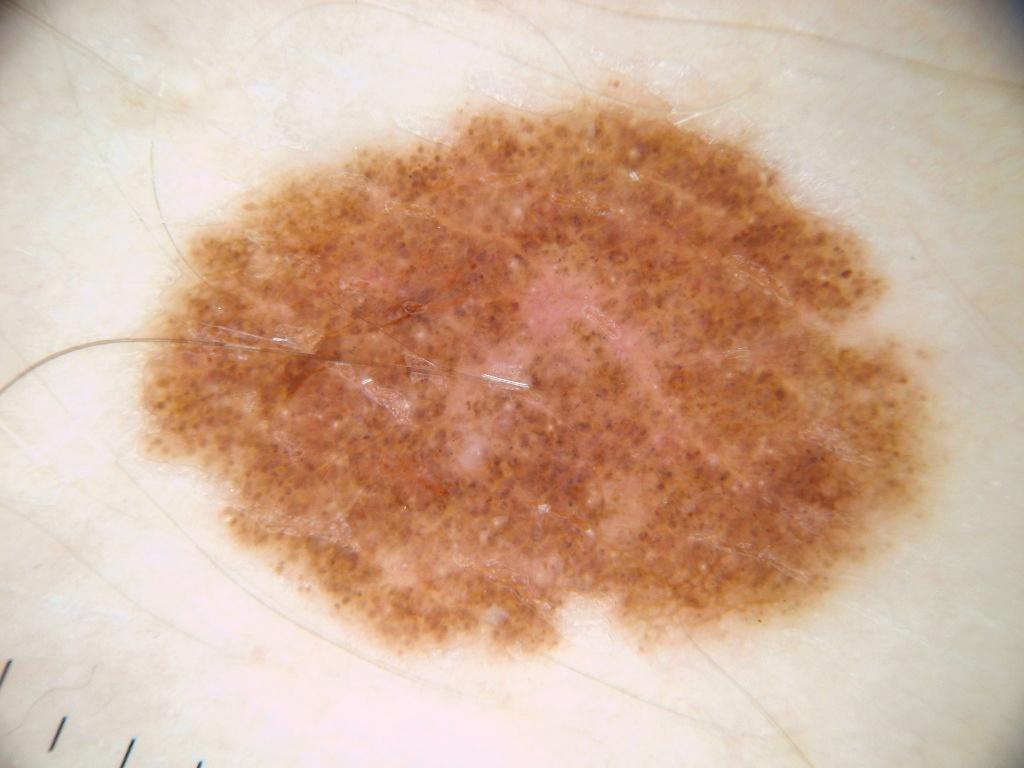Case summary: The subject is a male approximately 40 years of age. A dermatoscopic image of a skin lesion. A prominent lesion filling much of the field. The lesion spans left=141, top=80, right=966, bottom=651. Dermoscopy demonstrates globules, pigment network, and milia-like cysts, with no streaks or negative network. Conclusion: The clinical diagnosis was a melanocytic nevus, a benign lesion.